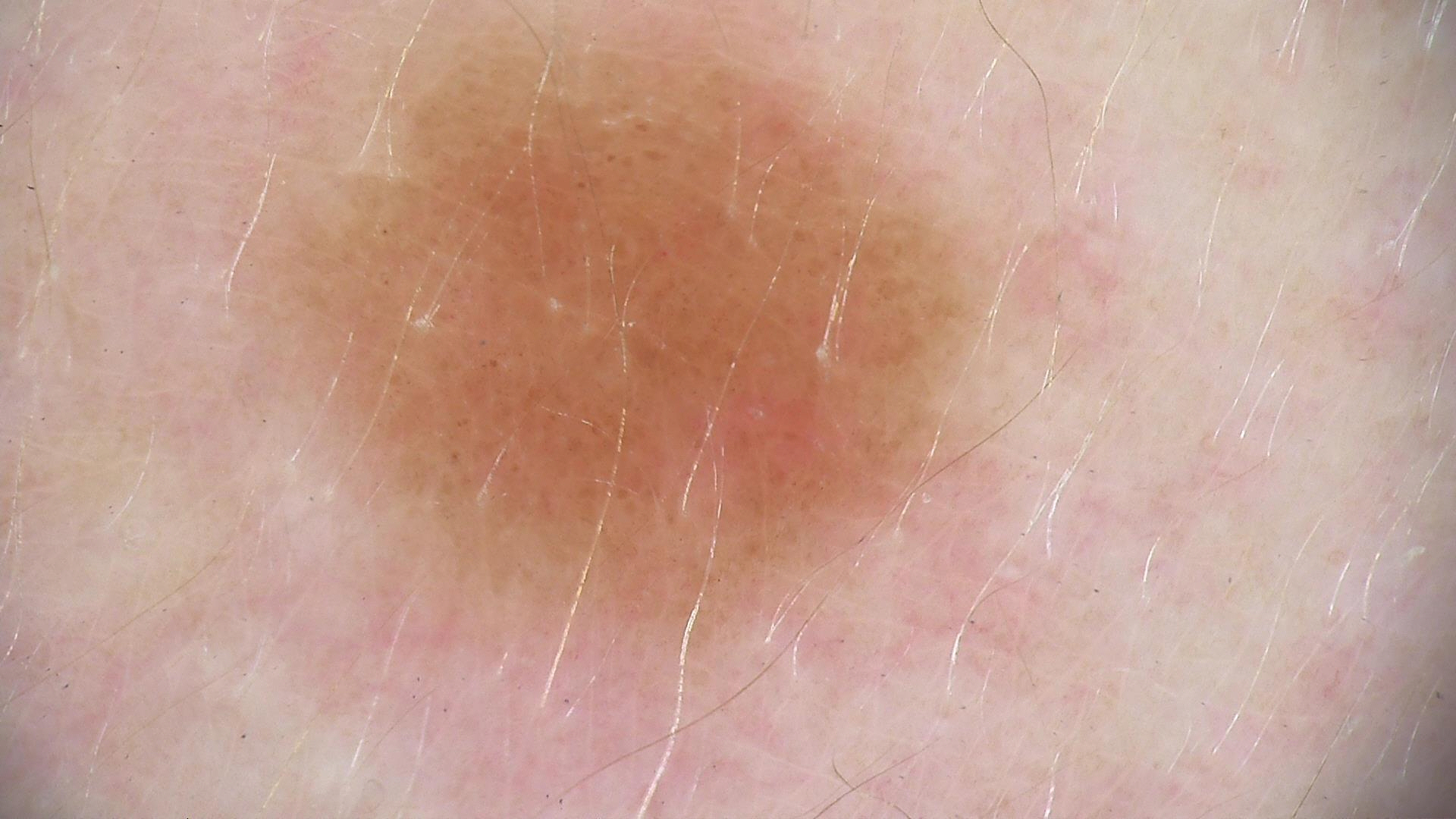A dermoscopic photograph of a skin lesion.
Consistent with a compound nevus.